The photograph was taken at a distance · present for one to four weeks · the patient reports the lesion is rough or flaky.
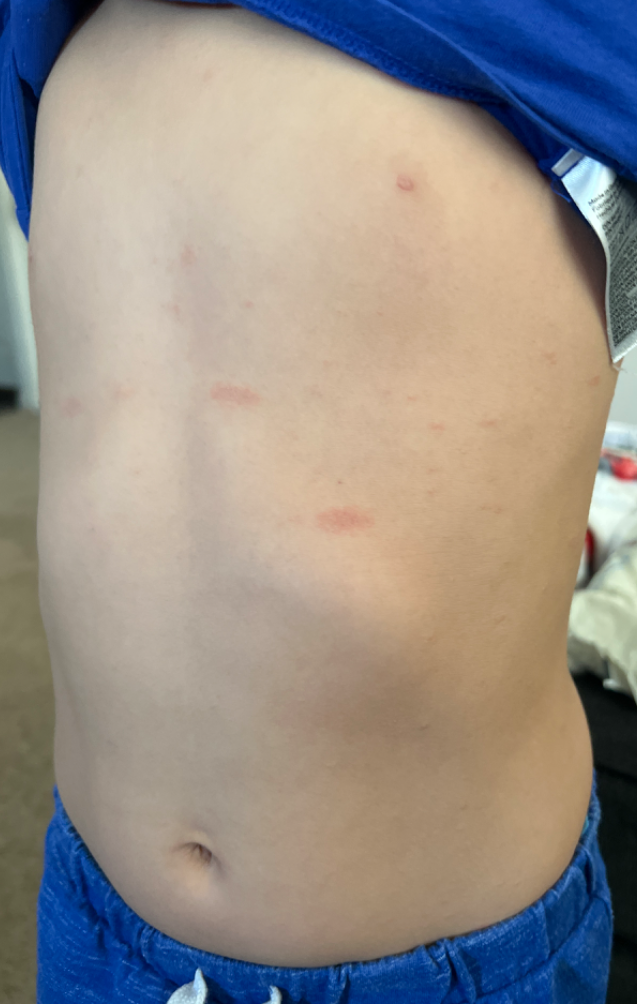  differential:
    leading:
      - Pityriasis rosea
    considered:
      - Eczema
      - Syphilis